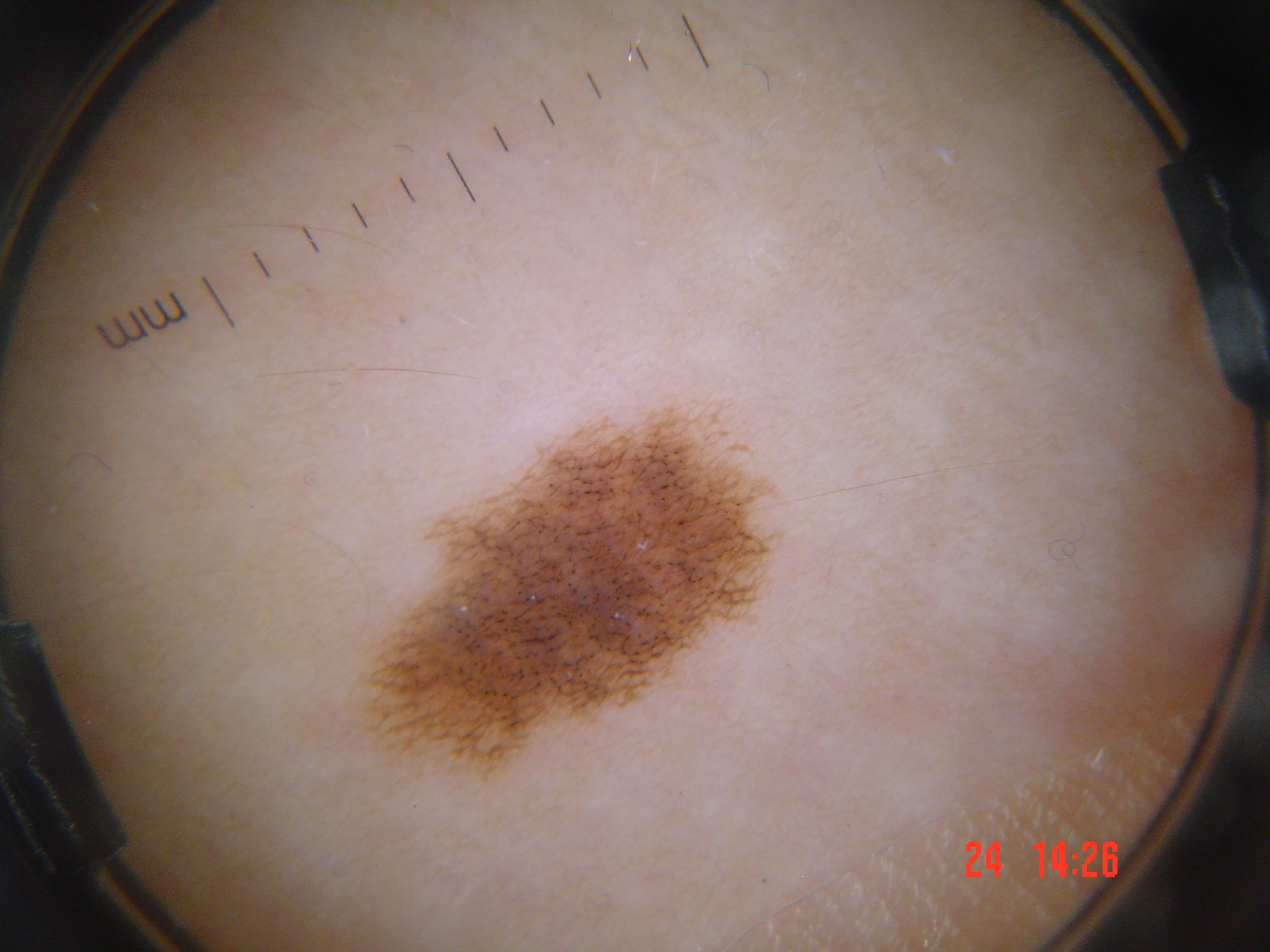A dermatoscopic image of a skin lesion.
The diagnosis was a benign lesion — a dysplastic junctional nevus.